A dermoscopic close-up of a skin lesion.
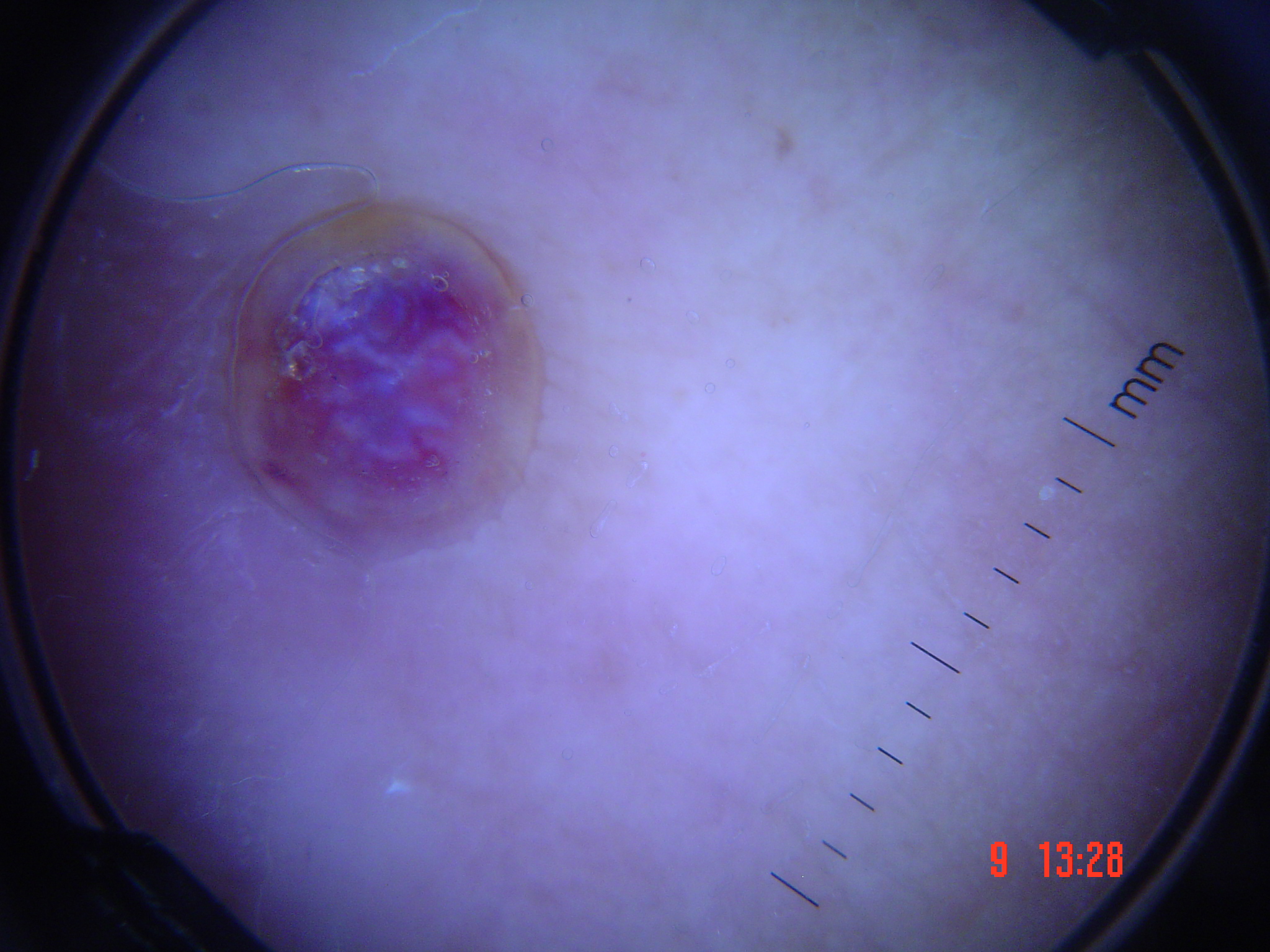{"lesion_type": {"main_class": "vascular"}, "diagnosis": {"name": "Kaposi sarcoma", "code": "ks", "malignancy": "malignant", "super_class": "non-melanocytic", "confirmation": "histopathology"}}